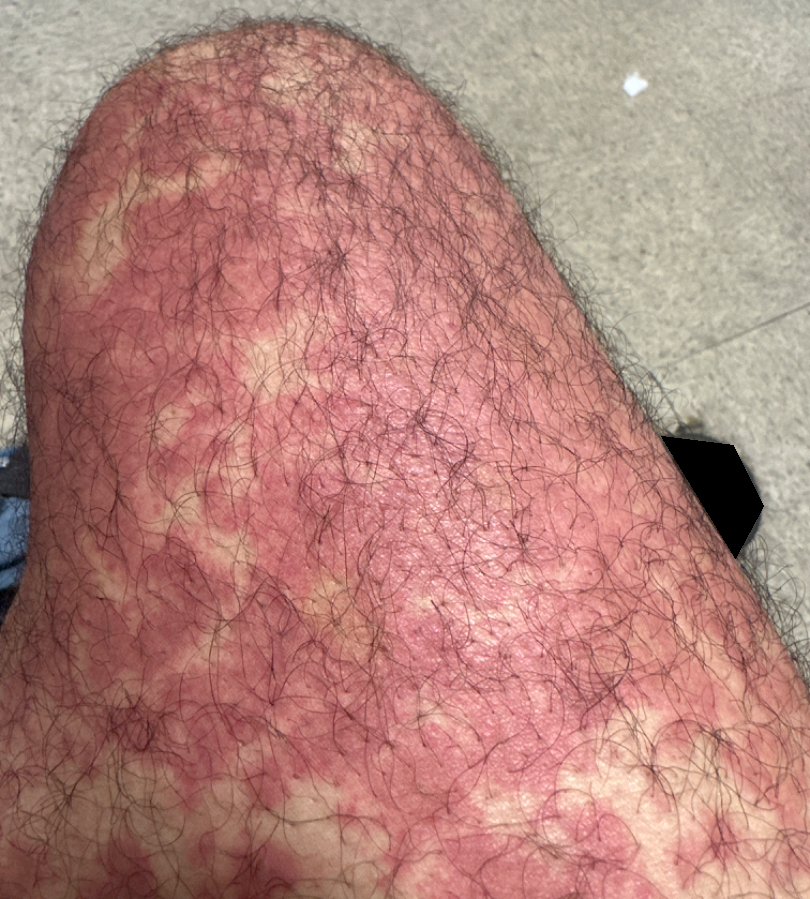The subject is male.
The lesion involves the leg.
A close-up photograph.
On teledermatology review, Drug Rash (possible); Vasculitis of the skin (possible); Rocky Mountain spotted fever (lower probability).